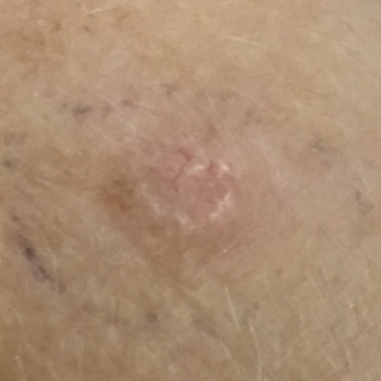image type: clinical photo | Fitzpatrick: II | patient: female, in their 50s | risk factors: prior malignancy (patient or family), tobacco use | lesion size: 6 × 5 mm | symptoms: bleeding, elevation, itching, growth | diagnostic label: basal cell carcinoma (biopsy-proven).